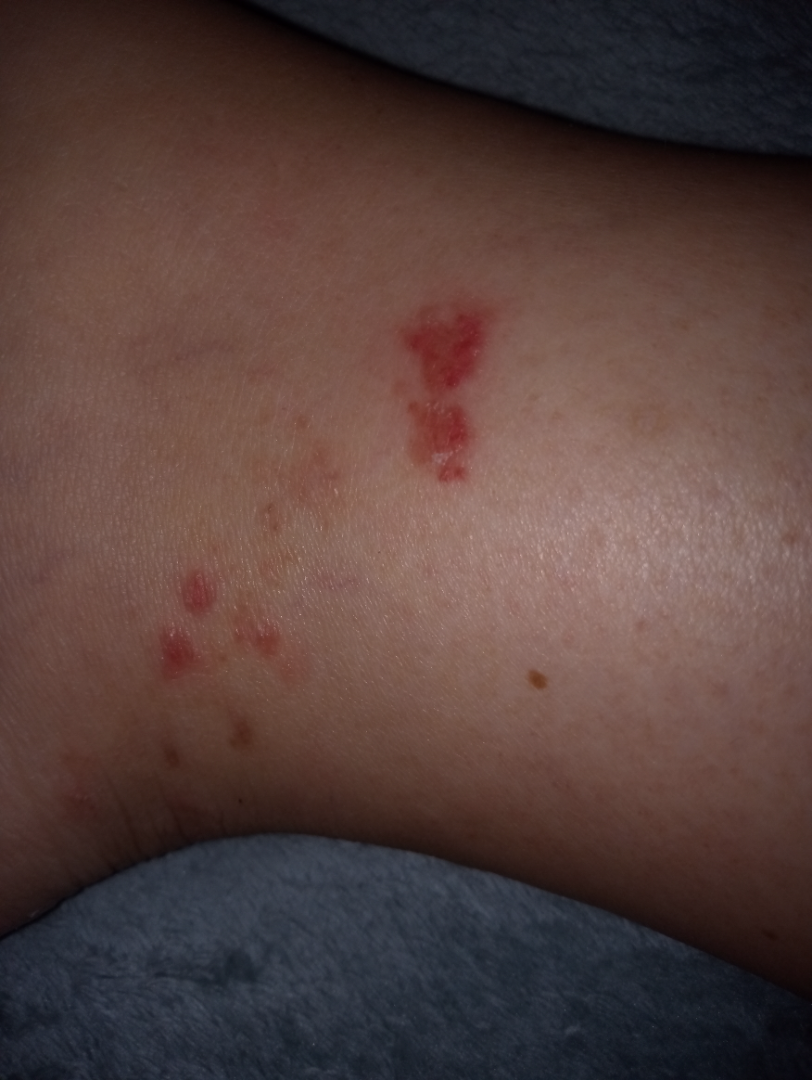Background: The affected area is the leg. The contributor is 30–39, female. Close-up view. Findings: Favoring Herpes Zoster; also on the differential is Pigmented purpuric eruption; an alternative is Allergic Contact Dermatitis.